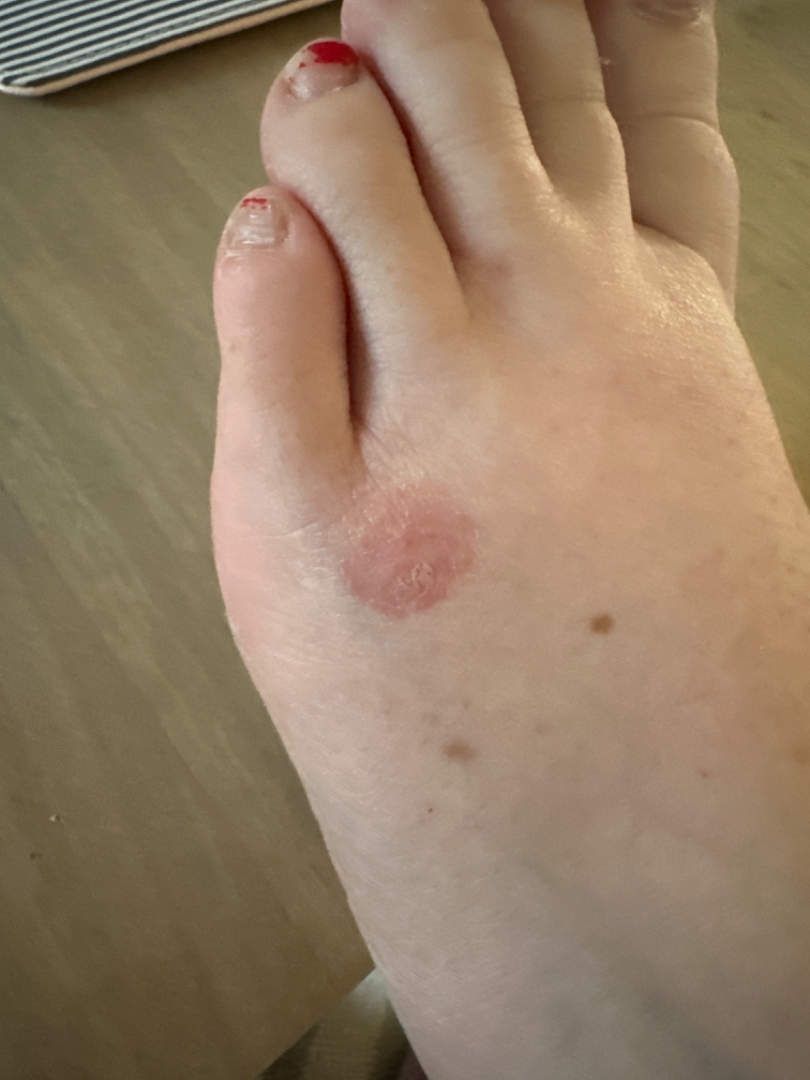The top or side of the foot is involved. Close-up view. The subject is 30–39, female. The differential, in no particular order, includes Acute and chronic dermatitis, Allergic Contact Dermatitis and Irritant Contact Dermatitis.